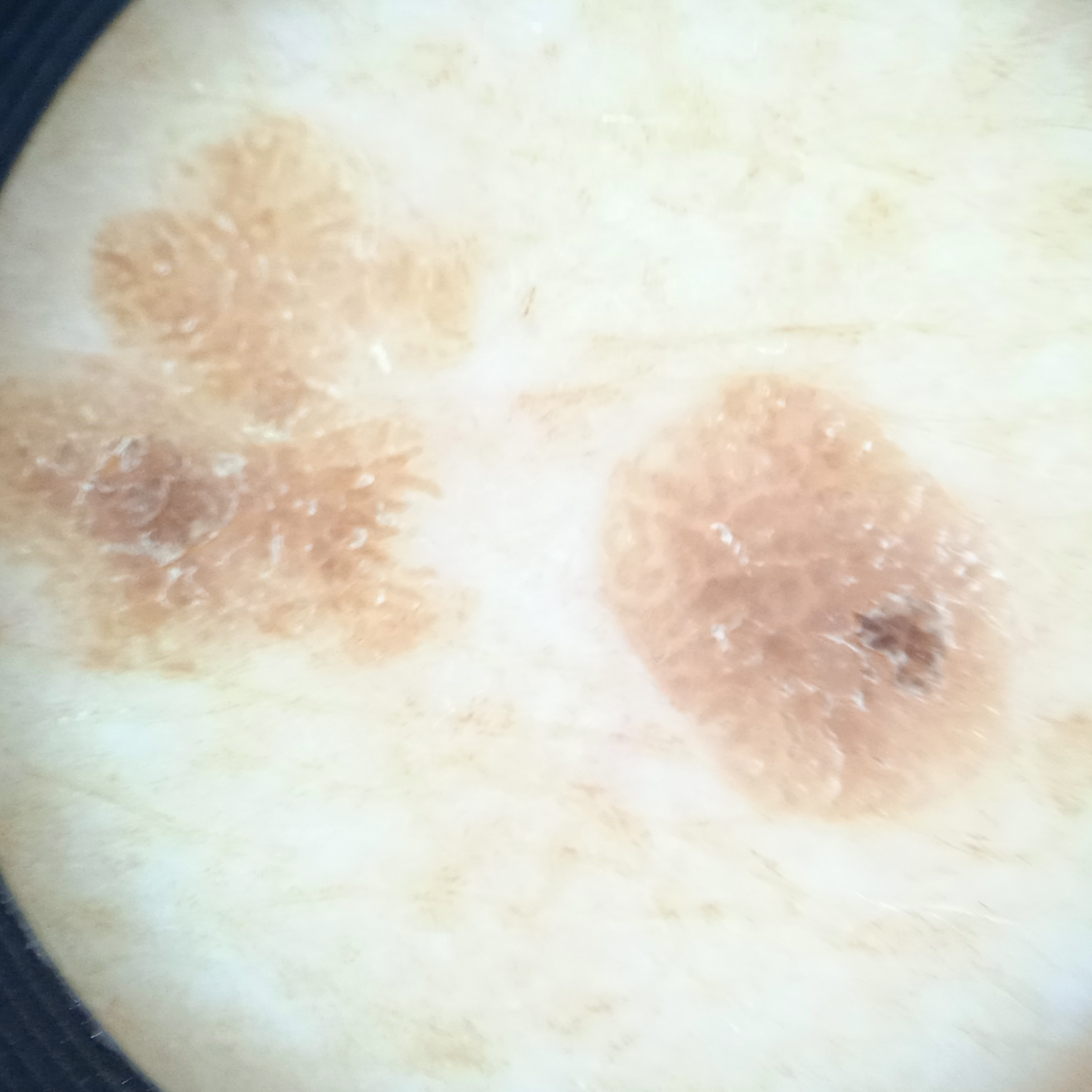Q: How does the patient's skin react to sun?
A: skin reddens painfully with sun exposure
Q: Why was this imaged?
A: research study (no referral diagnosis)
Q: What is the patient's nevus burden?
A: a moderate number of melanocytic nevi
Q: What are the relevant risk factors?
A: a personal history of cancer, immunosuppression, a personal history of skin cancer
Q: Patient demographics?
A: female, 72 years of age
Q: What kind of image is this?
A: dermatoscopic image
Q: Where is the lesion?
A: the back
Q: Lesion size?
A: 6.2 mm
Q: What was the diagnosis?
A: seborrheic keratosis (dermatologist consensus)